A close-up photograph. The condition has been present for less than one week. The top or side of the foot, back of the hand, back of the torso, head or neck, front of the torso and leg are involved. Self-categorized by the patient as a rash. The patient reports the lesion is flat: 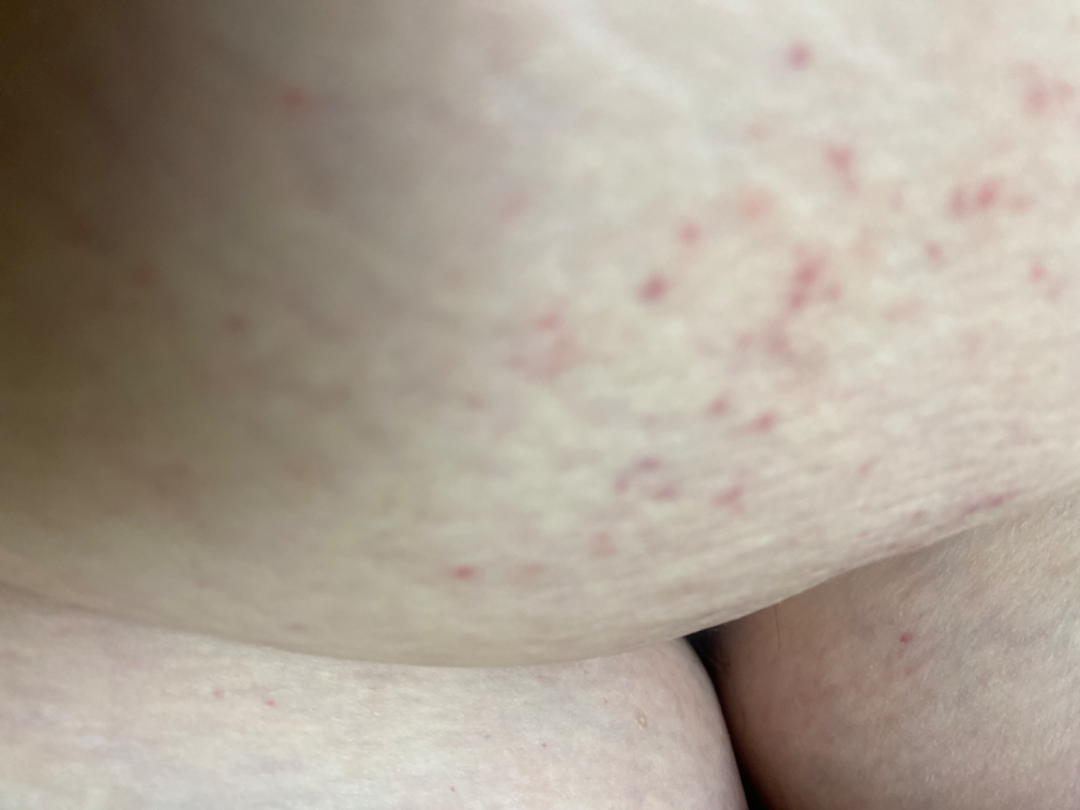The favored diagnosis is Folliculitis; also on the differential is Acne.